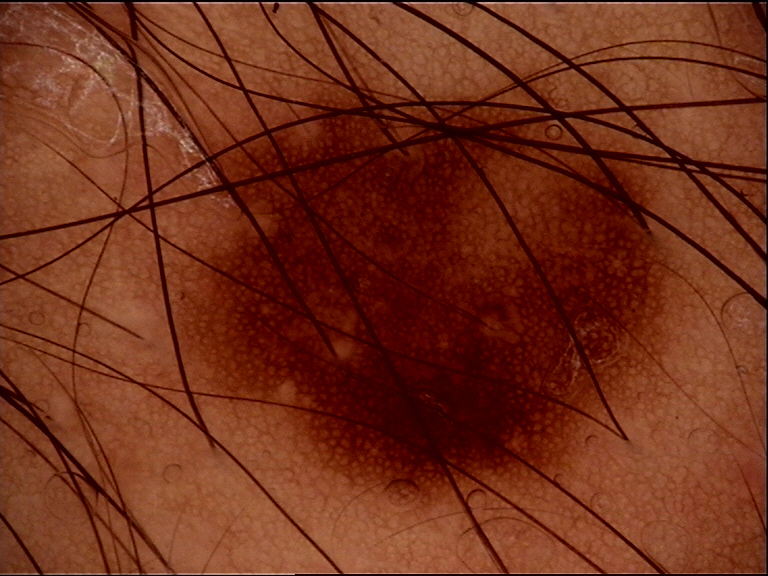Impression: The diagnosis was a banal lesion — a junctional nevus.